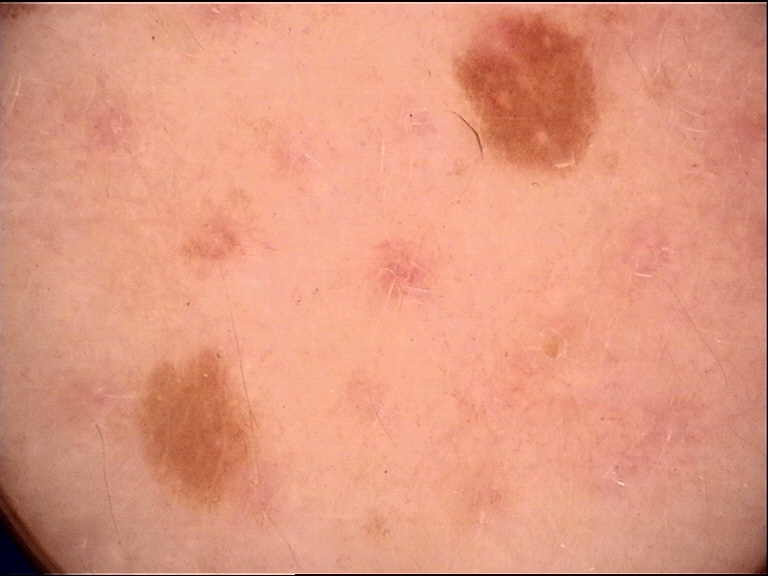A skin lesion imaged with a dermatoscope.
Consistent with a dysplastic junctional nevus.